A dermoscopic image of a skin lesion; a female patient aged 58-62:
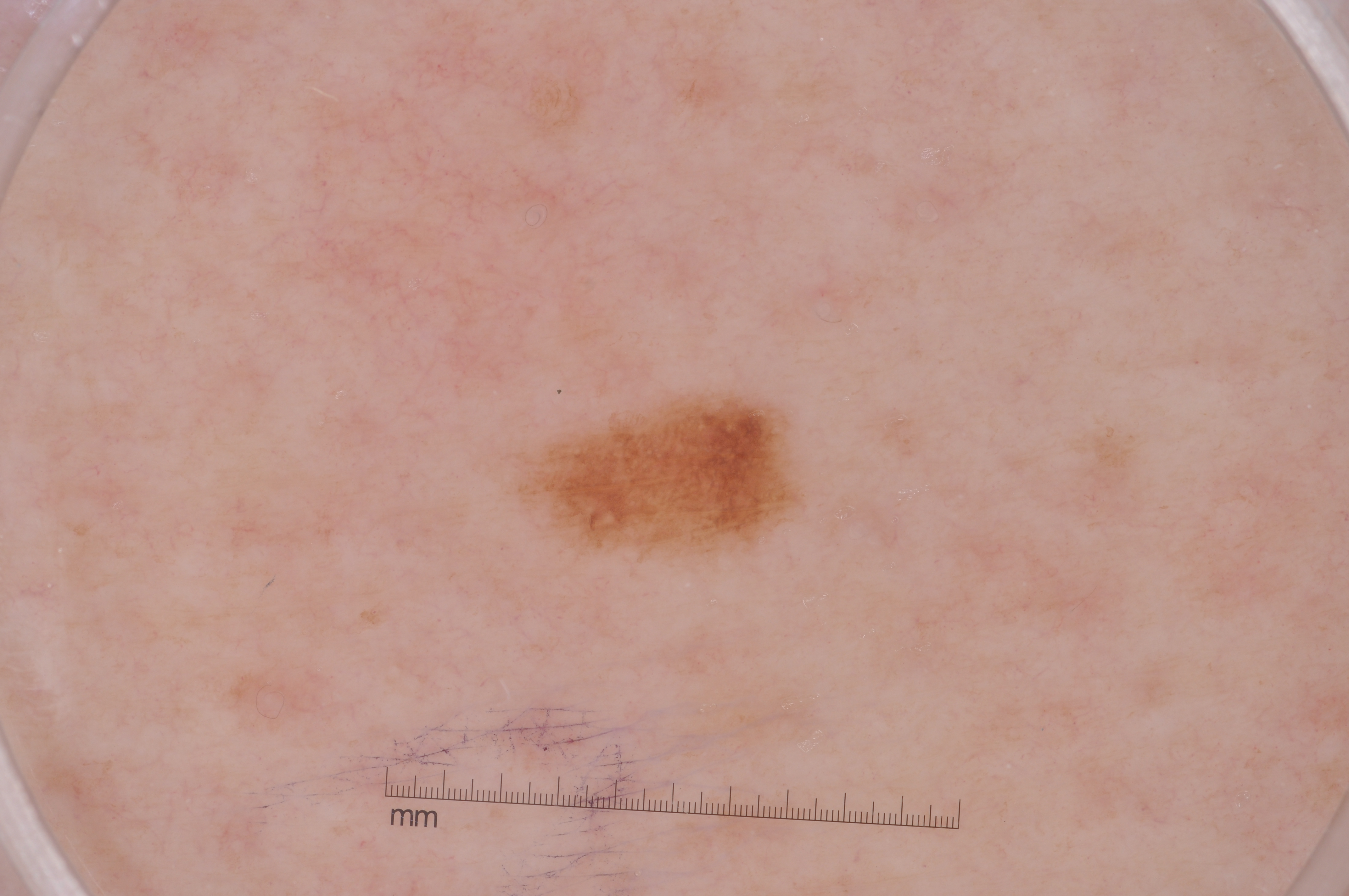dermoscopic pattern — pigment network
bounding box — bbox=[500, 387, 808, 565]
diagnosis — a melanocytic nevus